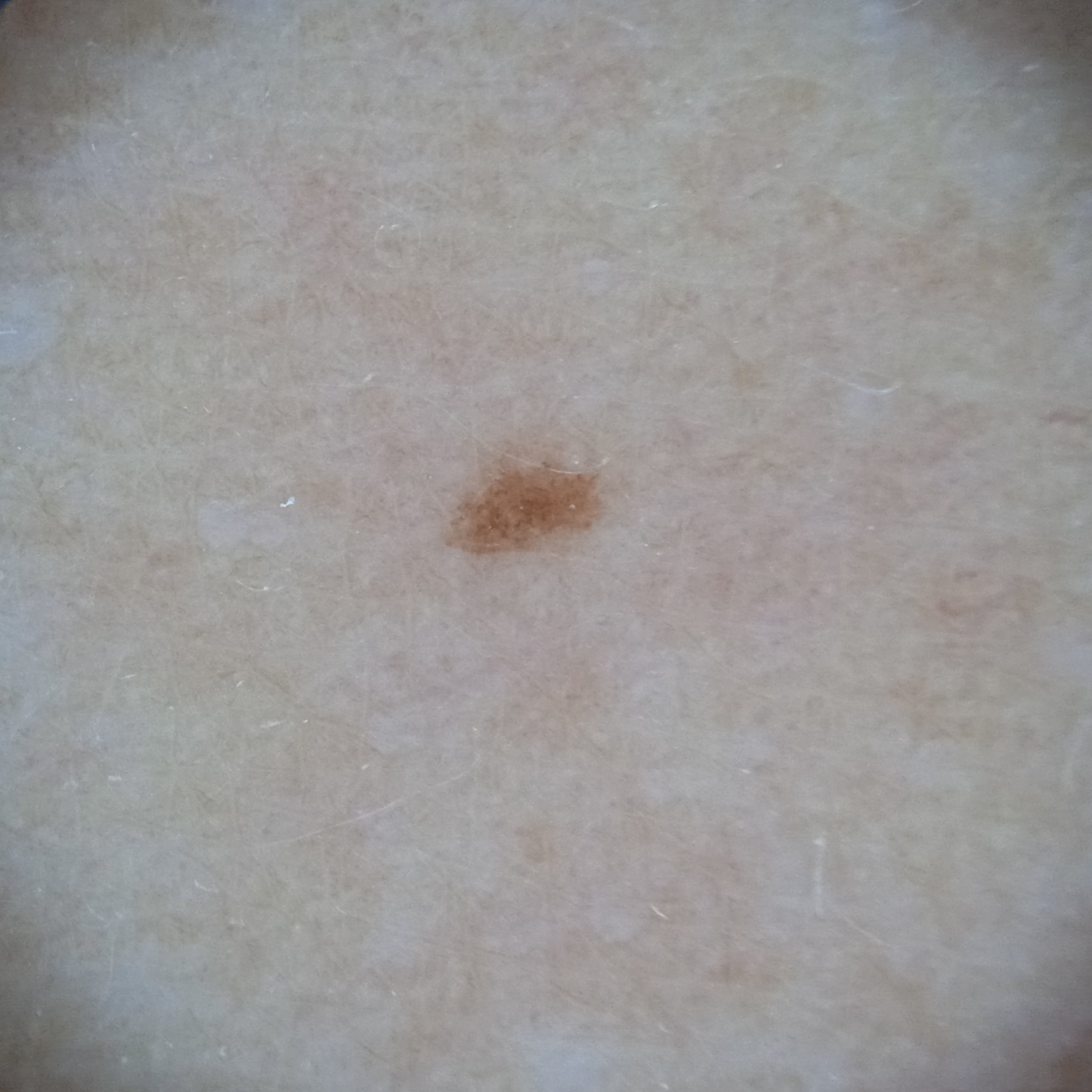diagnostic label = melanocytic nevus (dermatologist consensus)